A dermoscopy image of a single skin lesion.
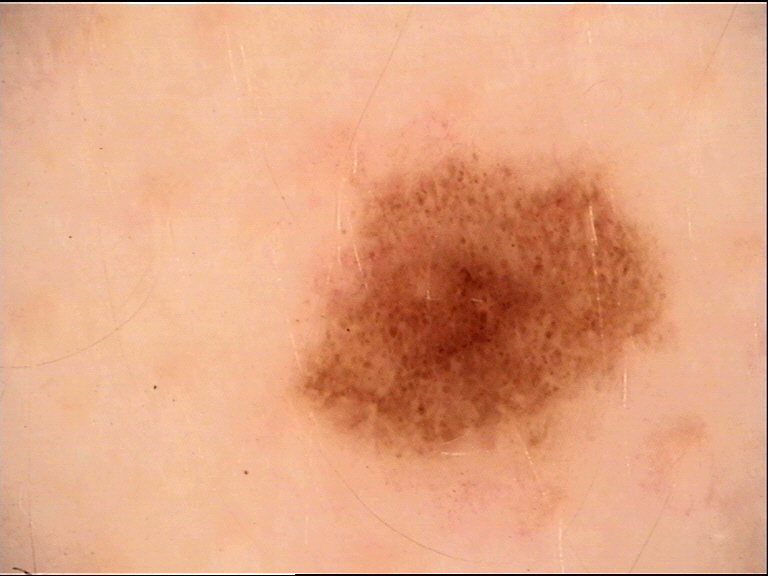* label · dysplastic compound nevus (expert consensus)